Close-up view · the lesion involves the leg.
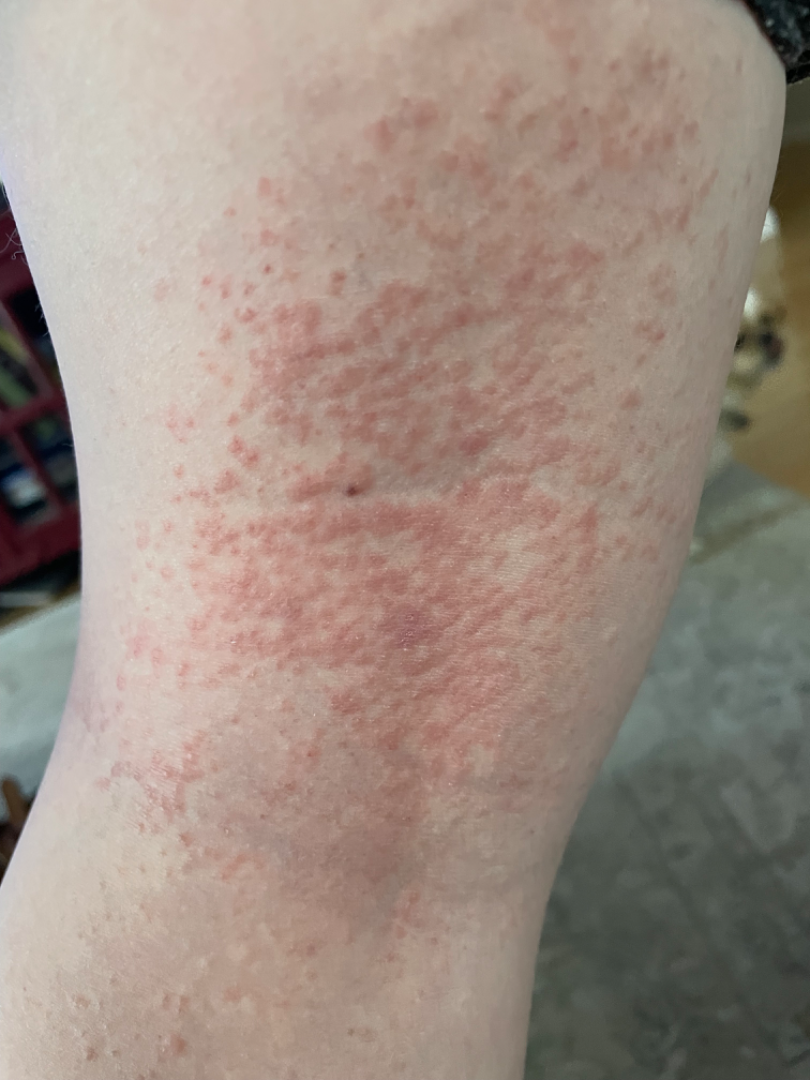Impression:
The differential includes Eczema and Allergic Contact Dermatitis, with no clear leading consideration.